Dermoscopy of a skin lesion.
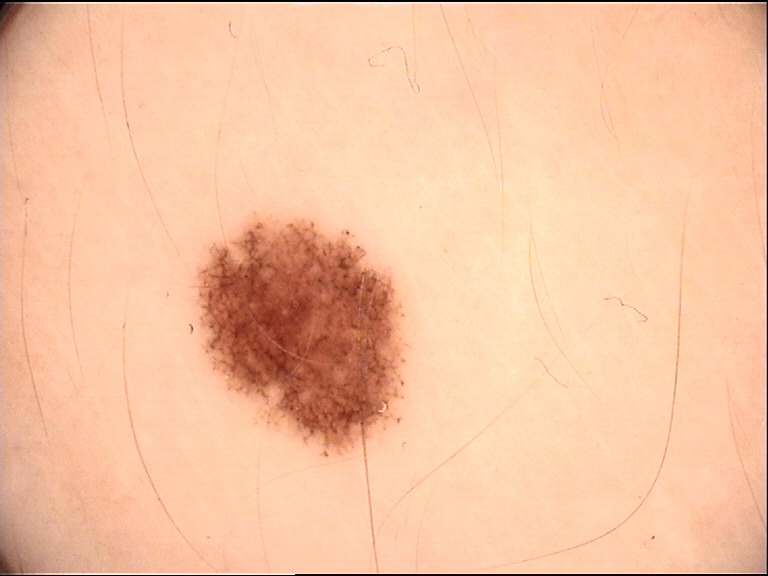The diagnosis was a dysplastic junctional nevus.